A clinical photograph showing a skin lesion. A male subject aged 79 — 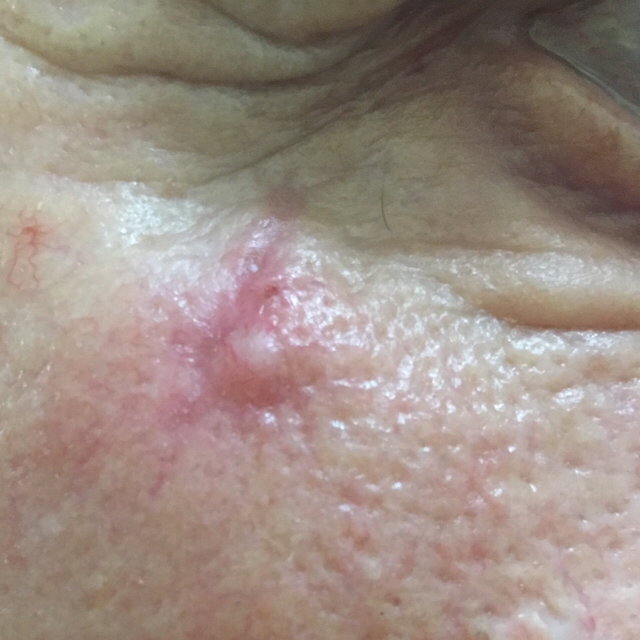The lesion involves the face. Per patient report, the lesion itches and is elevated, but has not grown. Confirmed on histopathology as a basal cell carcinoma.